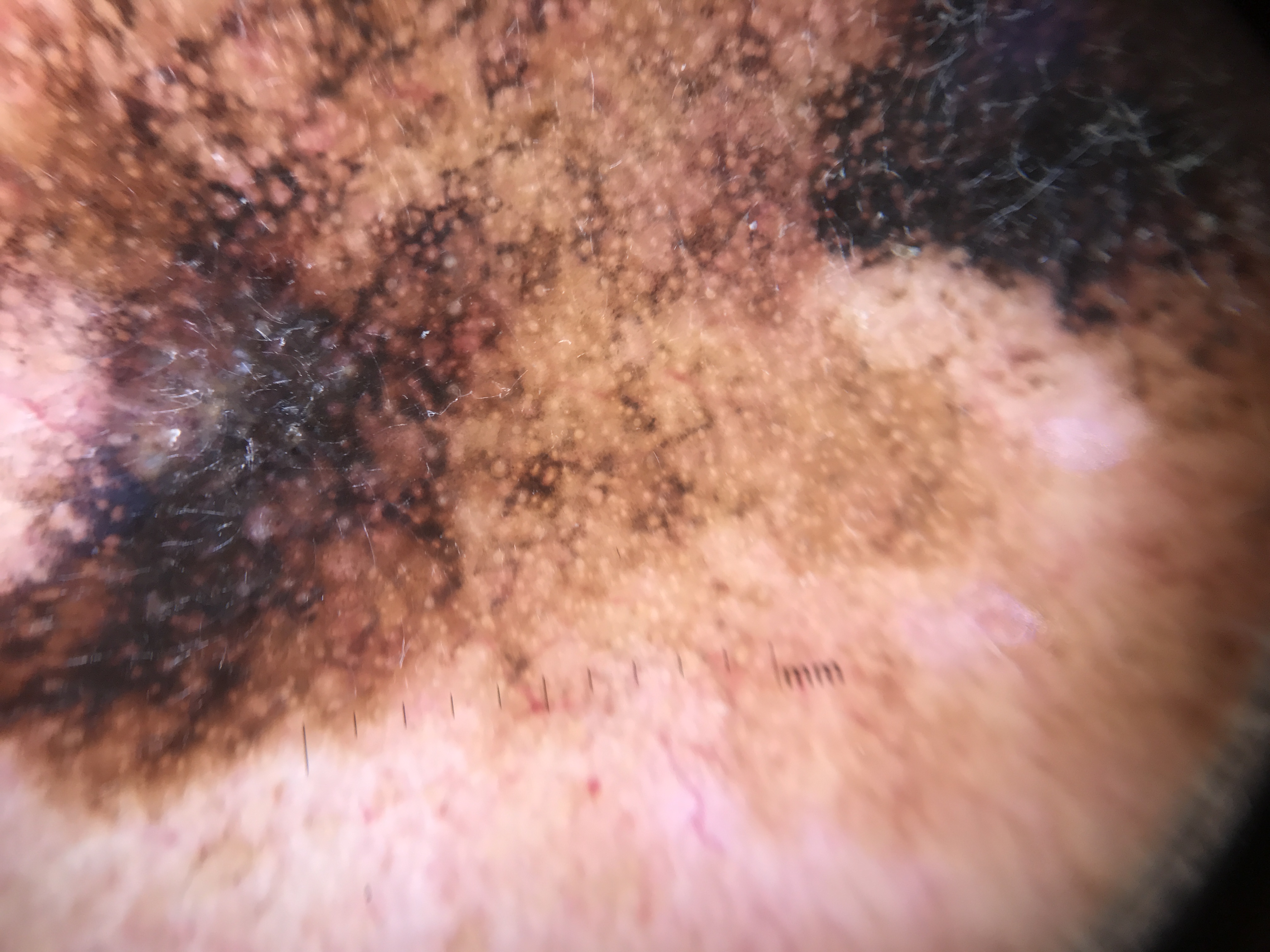diagnosis = lentigo maligna (biopsy-proven)